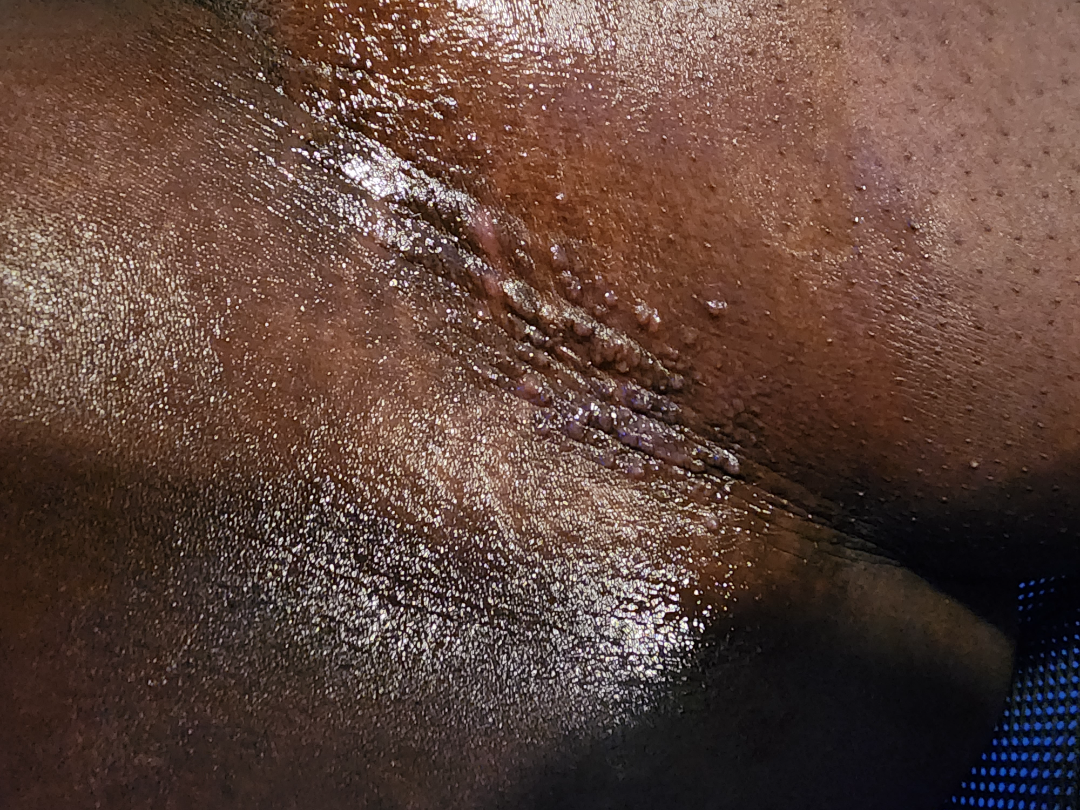Q: What was the assessment?
A: indeterminate from the photograph